A female patient about 15 years old, a skin lesion imaged with a dermatoscope:
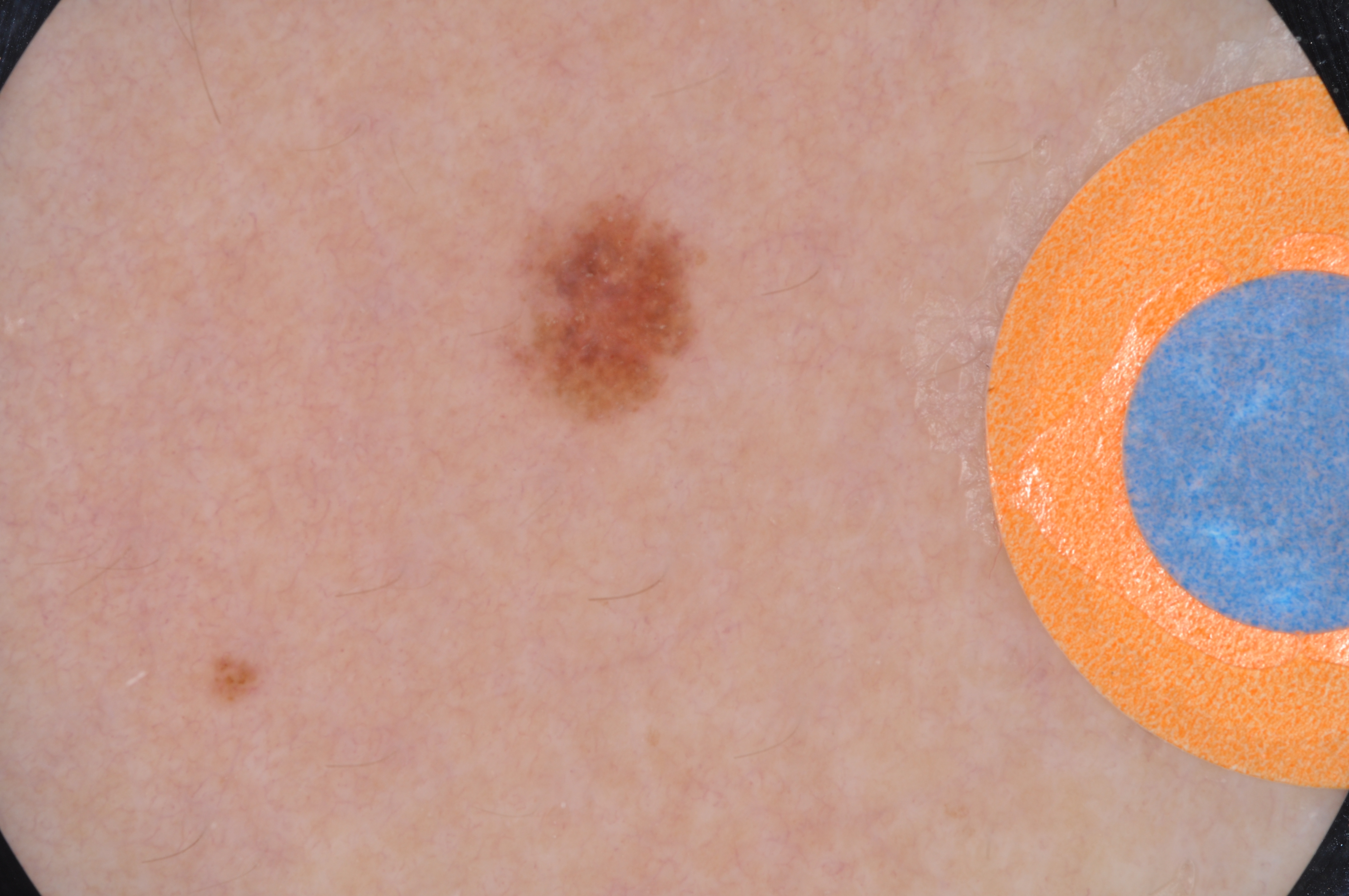Findings:
Dermoscopically, the lesion shows no pigment network, streaks, milia-like cysts, negative network, or globules. As (left, top, right, bottom), the lesion occupies the region [496, 181, 707, 434].
Assessment:
The clinical diagnosis was a melanocytic nevus.